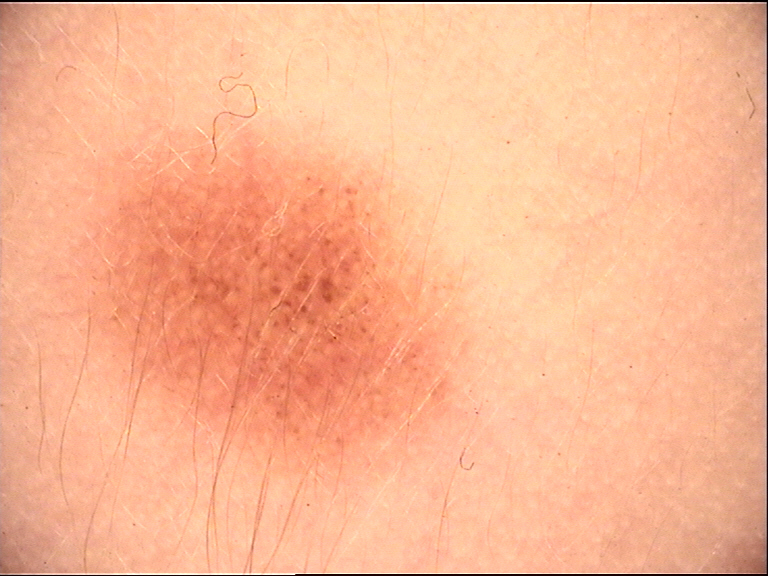image type — dermoscopy | diagnosis — congenital junctional nevus (expert consensus).